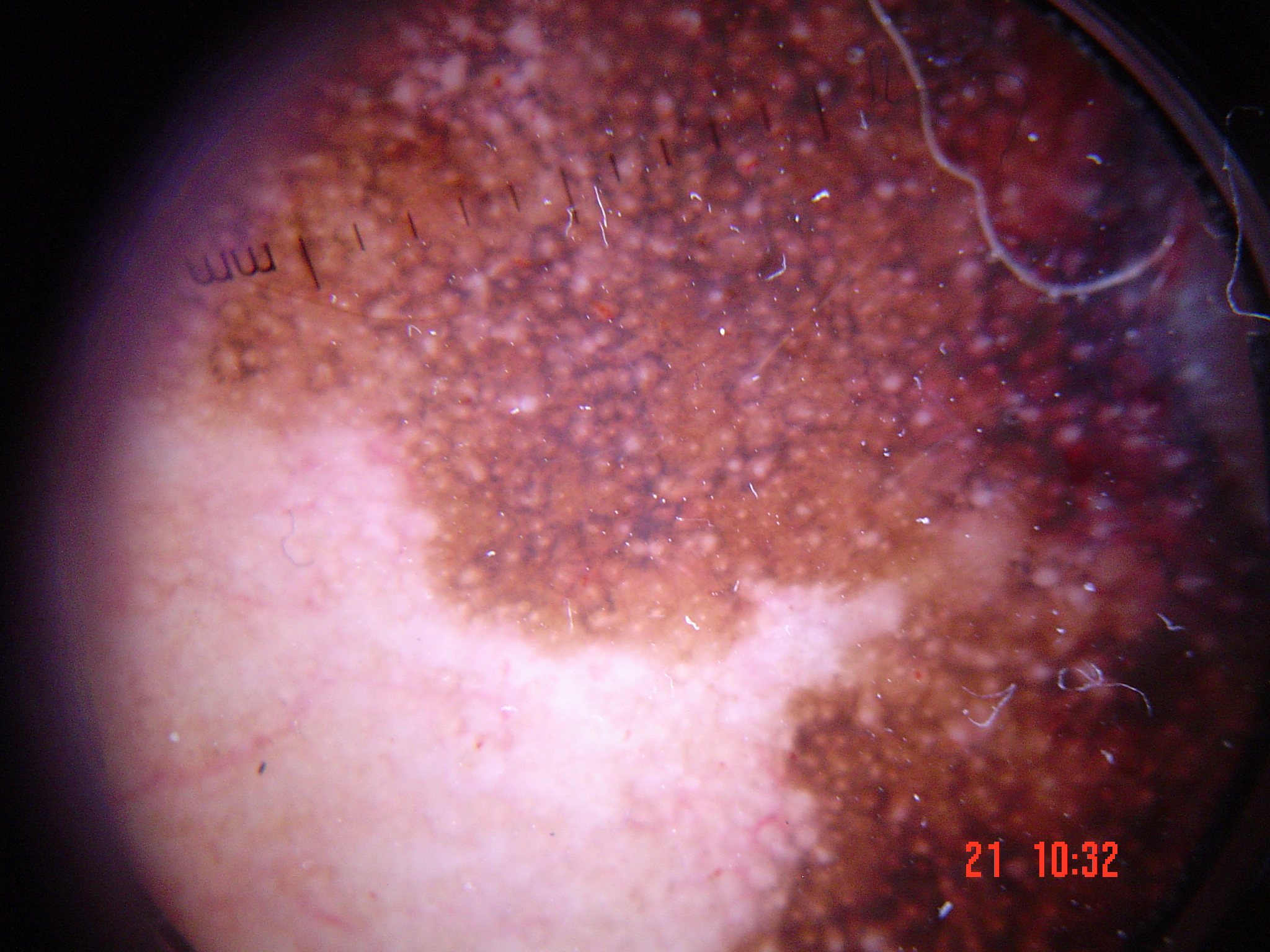A dermoscopic close-up of a skin lesion. Biopsy-confirmed as a lentigo maligna.